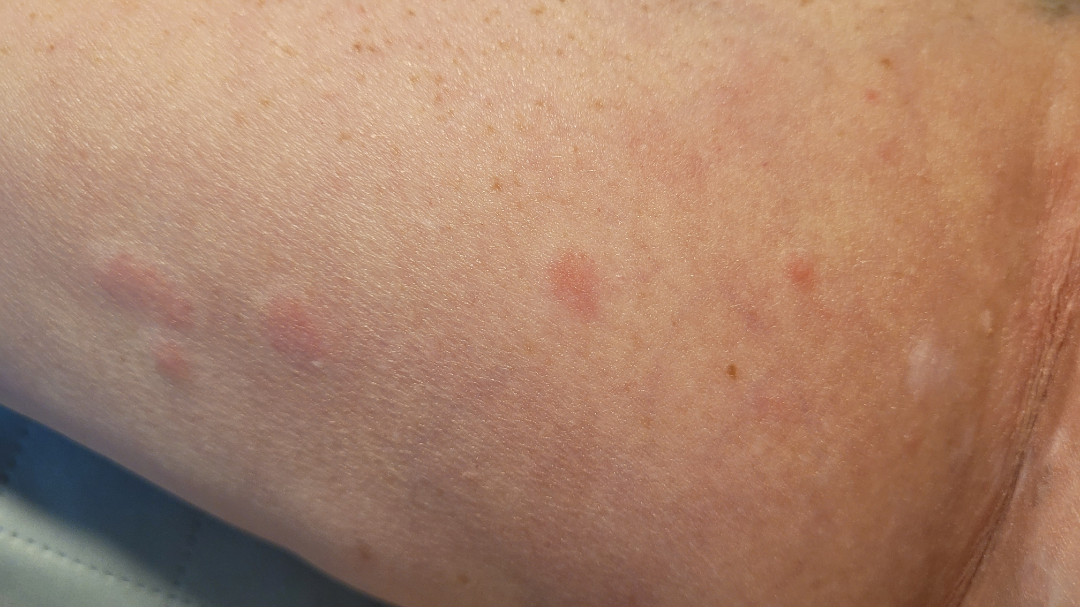{"body_site": "arm", "patient": "female, age 50–59", "shot_type": "close-up", "differential": {"tied_lead": ["Eczema", "Allergic Contact Dermatitis", "Urticaria", "Insect Bite"]}}